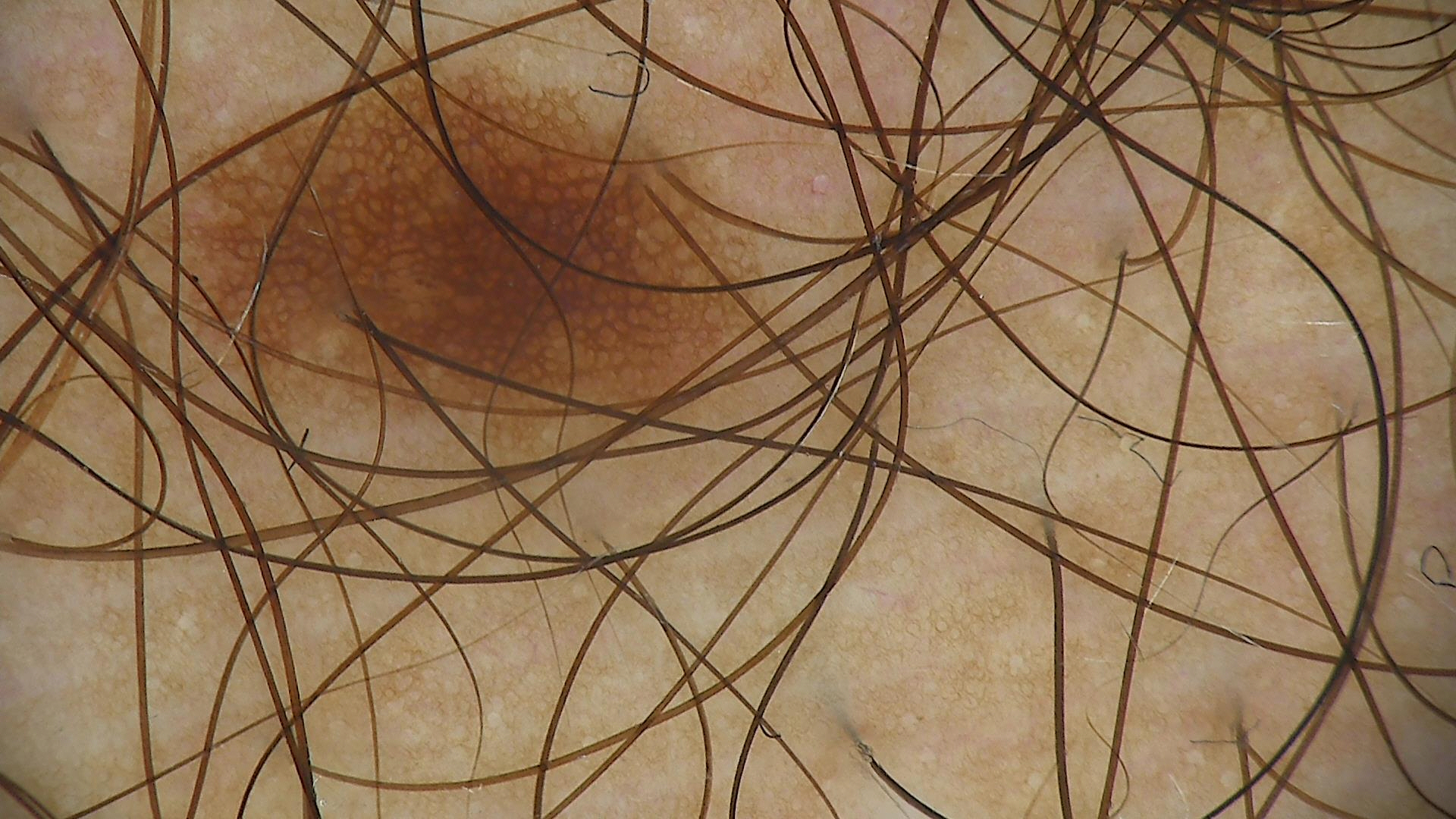{"image": "dermoscopy", "diagnosis": {"name": "junctional nevus", "code": "jb", "malignancy": "benign", "super_class": "melanocytic", "confirmation": "expert consensus"}}